A clinical photo of a skin lesion taken with a smartphone. A patient 58 years old — 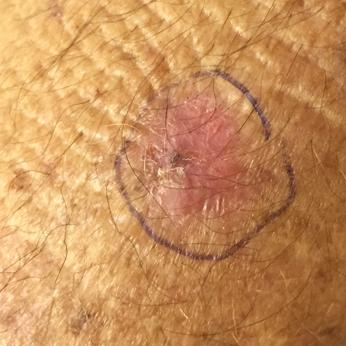The lesion was found on the neck.
The patient reports that the lesion has bled and itches.
The clinical impression was an actinic keratosis.